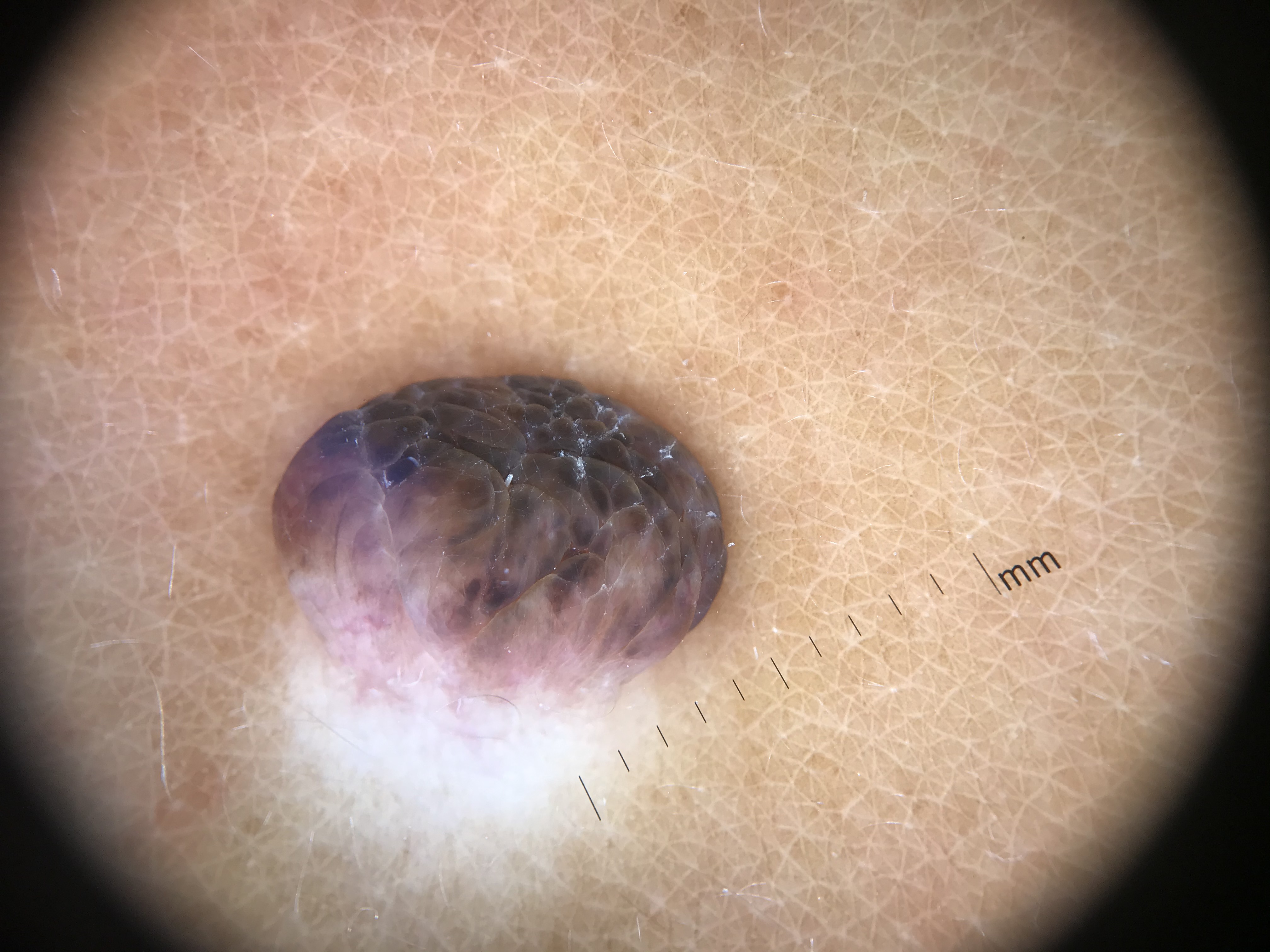imaging: dermoscopy, category: banal, diagnostic label: dermal nevus (expert consensus).